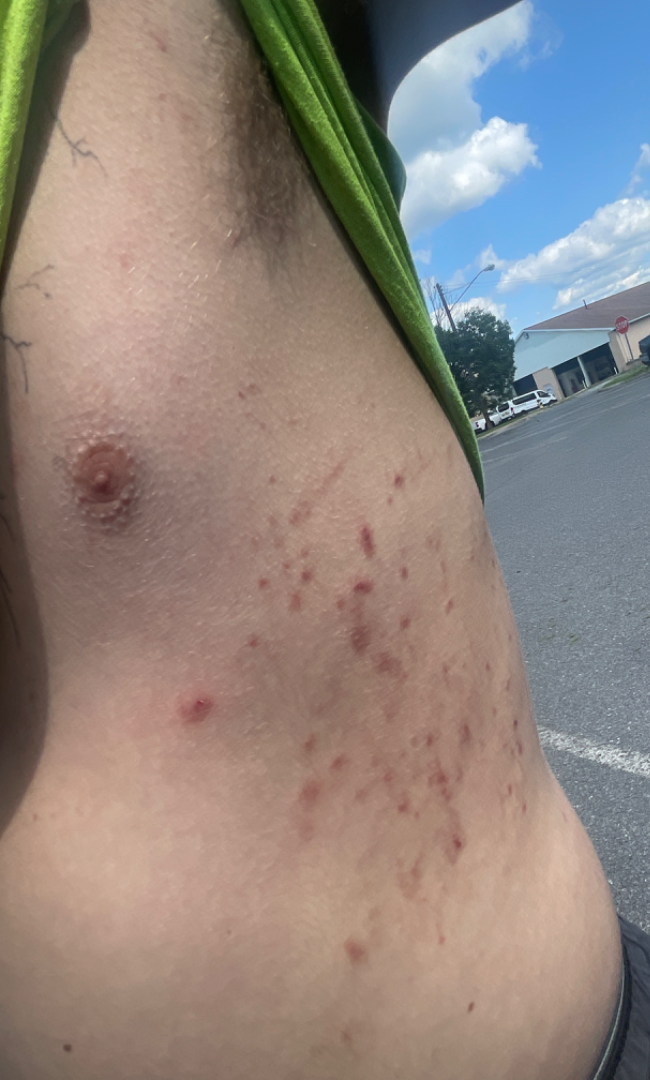Q: Image view?
A: at a distance
Q: Where on the body?
A: head or neck, front of the torso, arm and back of the hand
Q: What is the differential diagnosis?
A: reviewed remotely by one dermatologist: most likely Acne; also on the differential is Folliculitis